FST II. A female subject approximately 45 years of age.
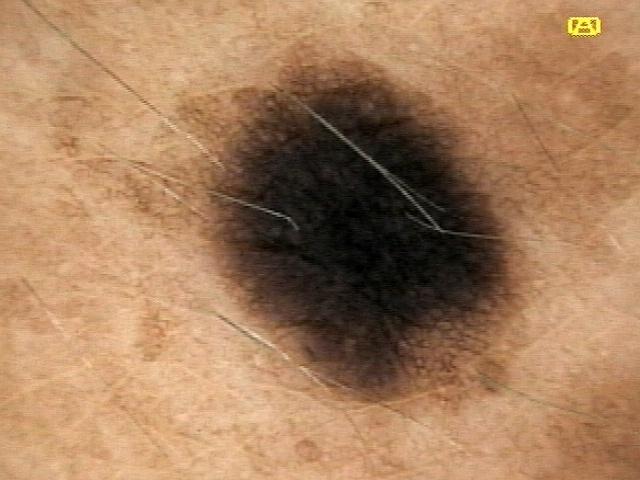The lesion is on the trunk, specifically the anterior trunk.
The biopsy diagnosis was a melanocytic lesion — a nevus.